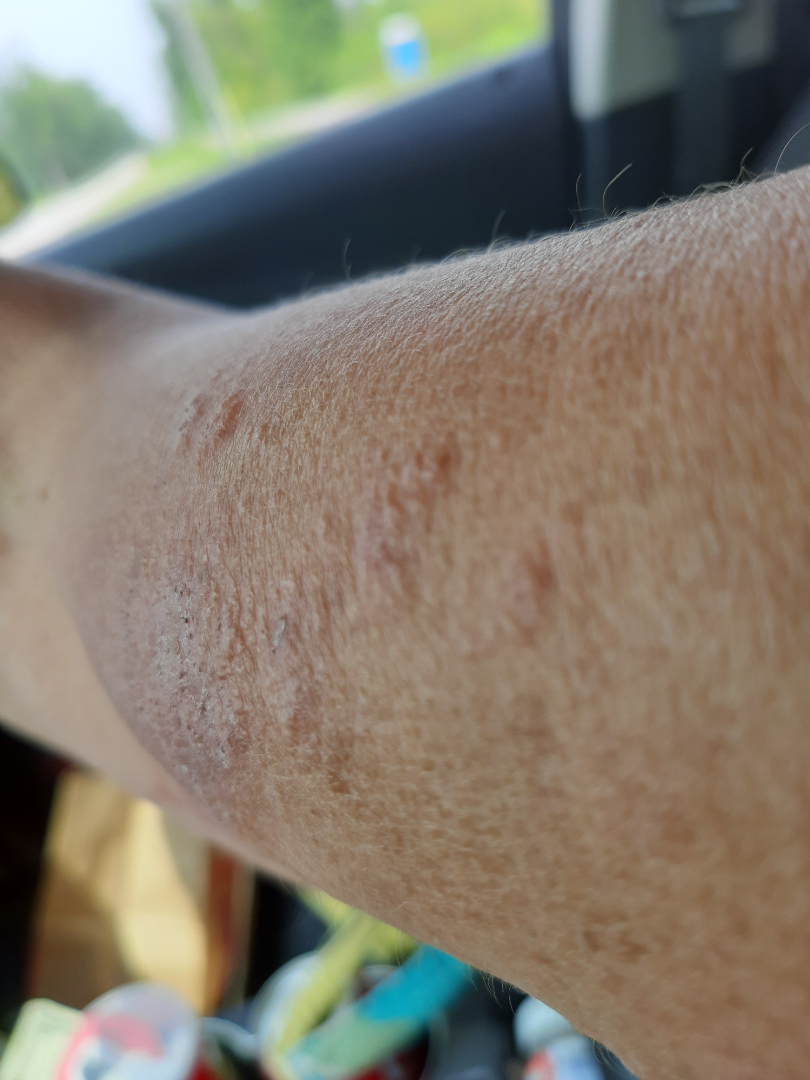site = arm and front of the torso | present for = one to four weeks | subject = female, age 60–69 | other reported symptoms = joint pain and fatigue | described texture = raised or bumpy and rough or flaky | image framing = at a distance | self-categorized as = skin that appeared healthy to them | symptoms = itching, burning and enlargement | diagnostic considerations = reviewed remotely by one dermatologist: in keeping with Chronic dermatitis, NOS.